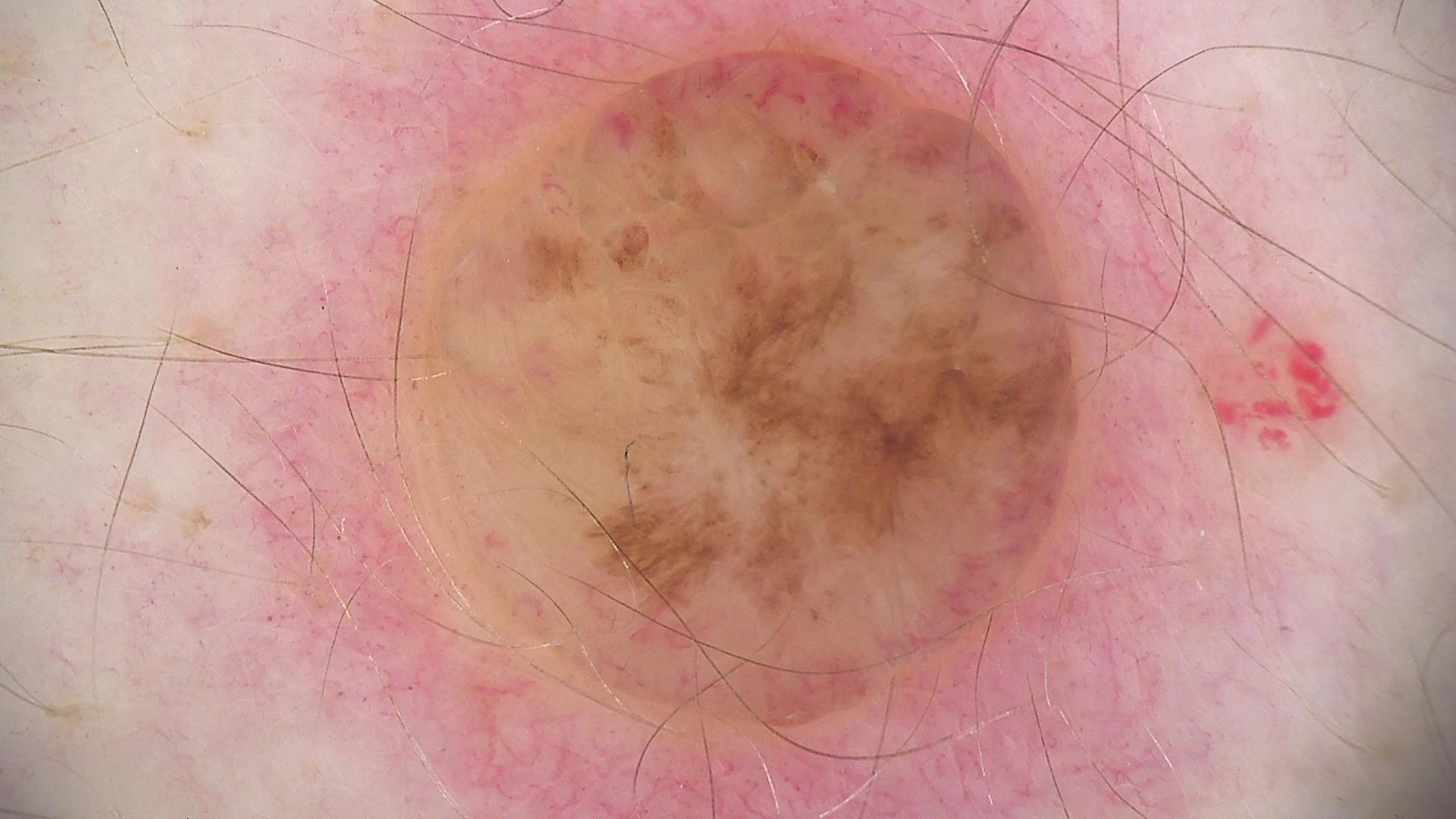image — dermatoscopy | subtype — banal | class — dermal nevus (expert consensus).